The patient indicates the lesion is flat, the patient described the issue as a rash, located on the leg, the photo was captured at an angle, the condition has been present for less than one week, the subject is female, no relevant systemic symptoms — 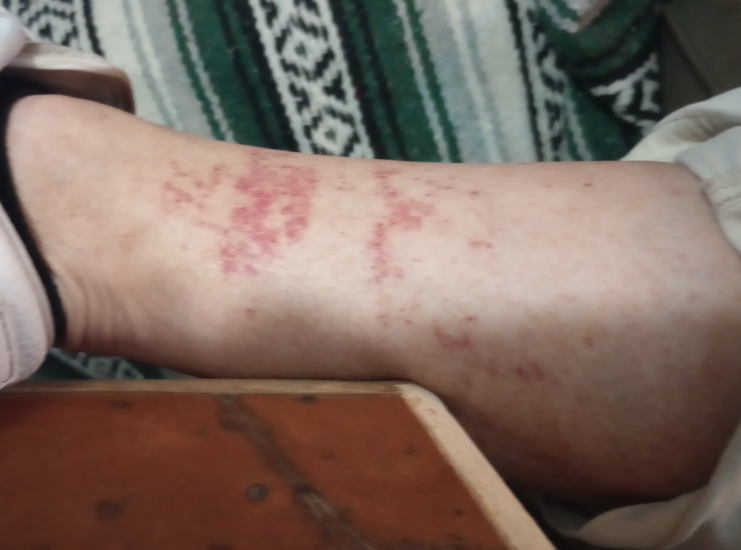{
  "differential": {
    "leading": [
      "Pigmented purpuric eruption"
    ],
    "unlikely": [
      "Contact dermatitis",
      "Stasis Dermatitis"
    ]
  }
}